A dermoscopic image of a skin lesion.
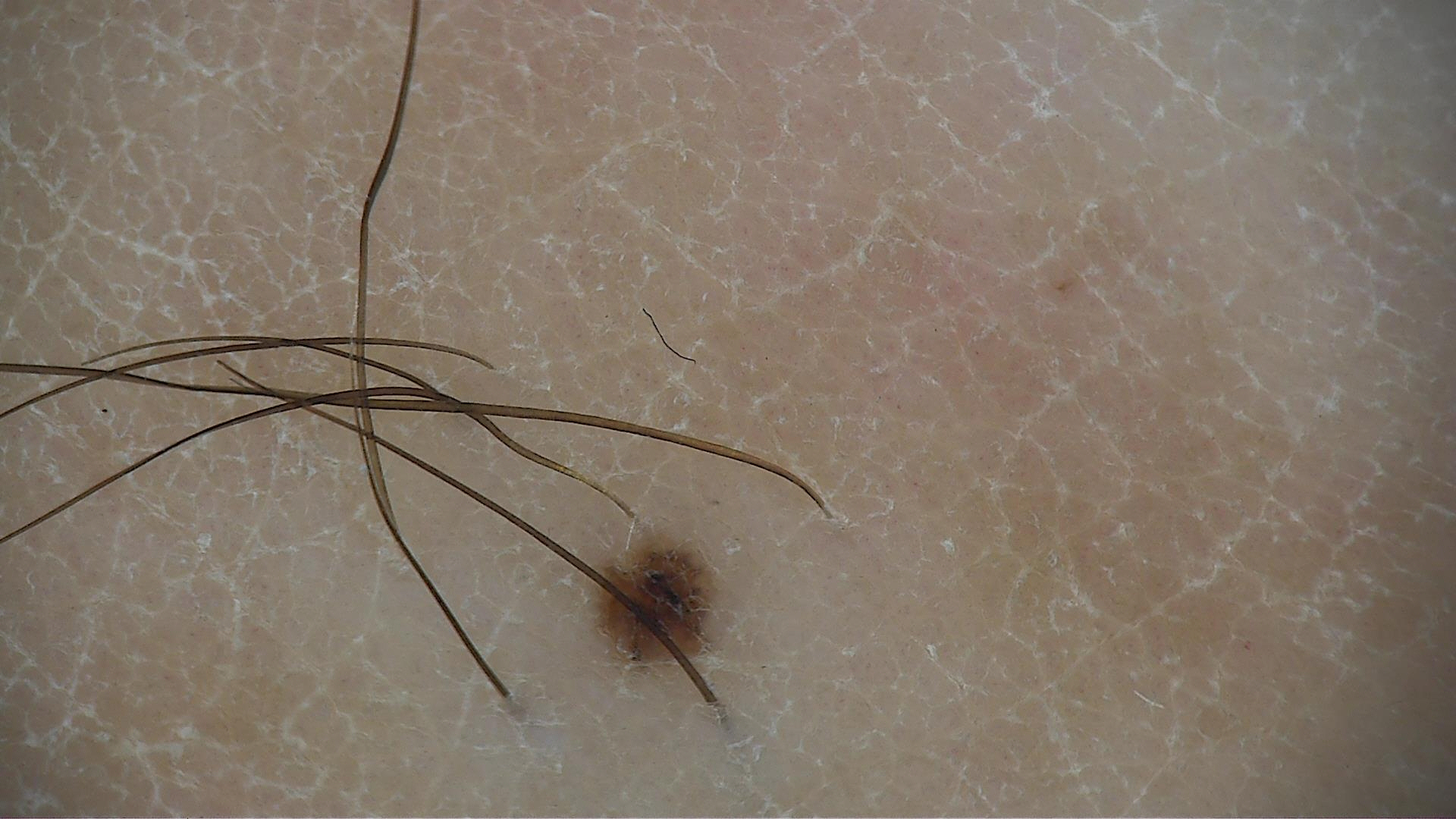class: junctional nevus (expert consensus)